A dermoscopic photograph of a skin lesion.
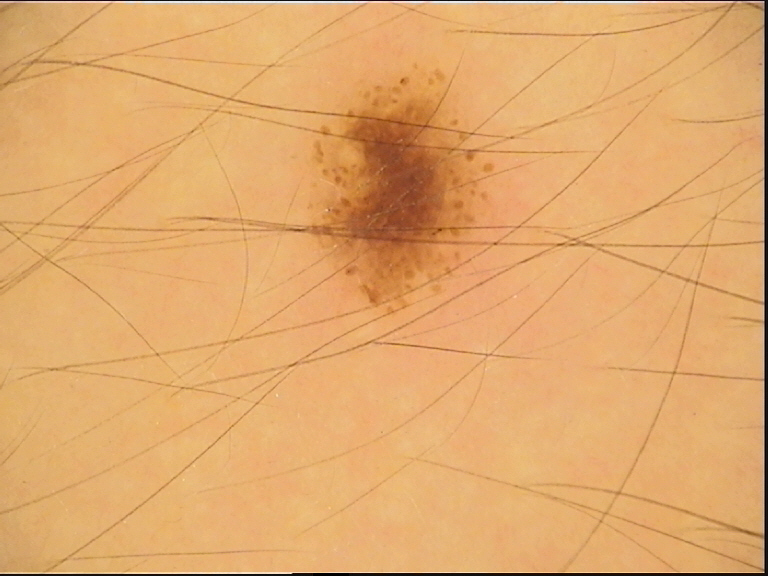label=dysplastic junctional nevus (expert consensus).